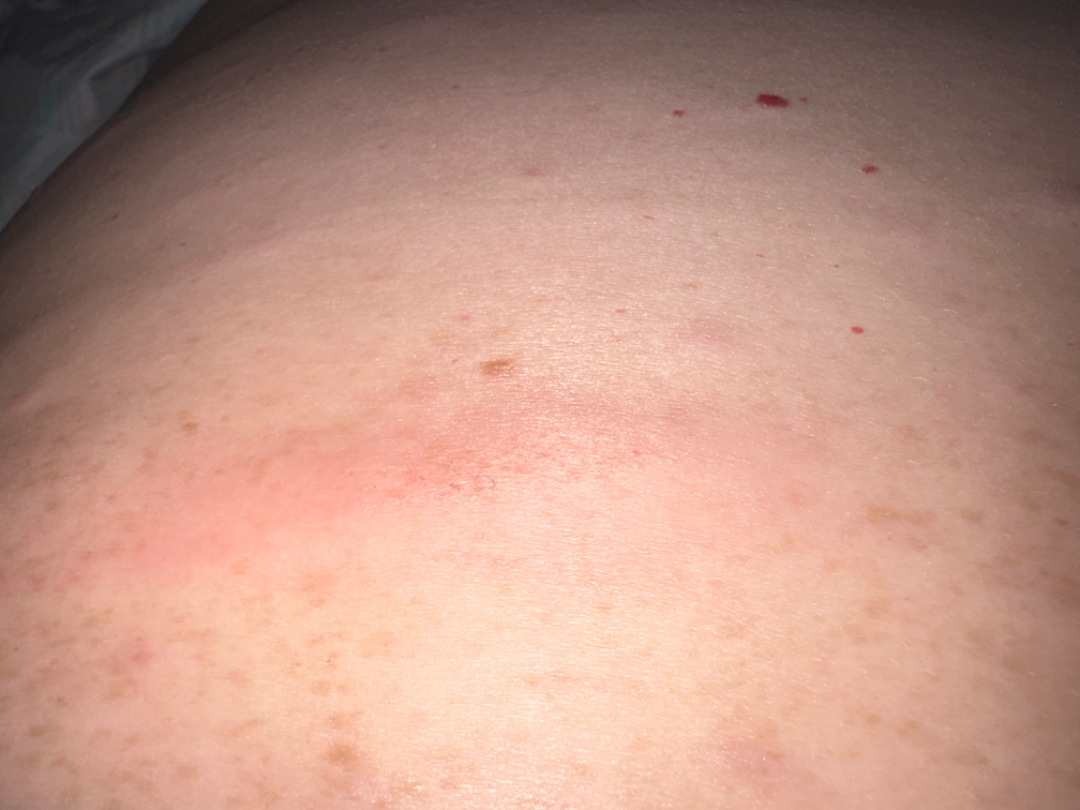image framing=close-up
diagnostic considerations=the differential, in no particular order, includes Abscess and Cellulitis